Recorded as Fitzpatrick I. A male patient in their 60s: 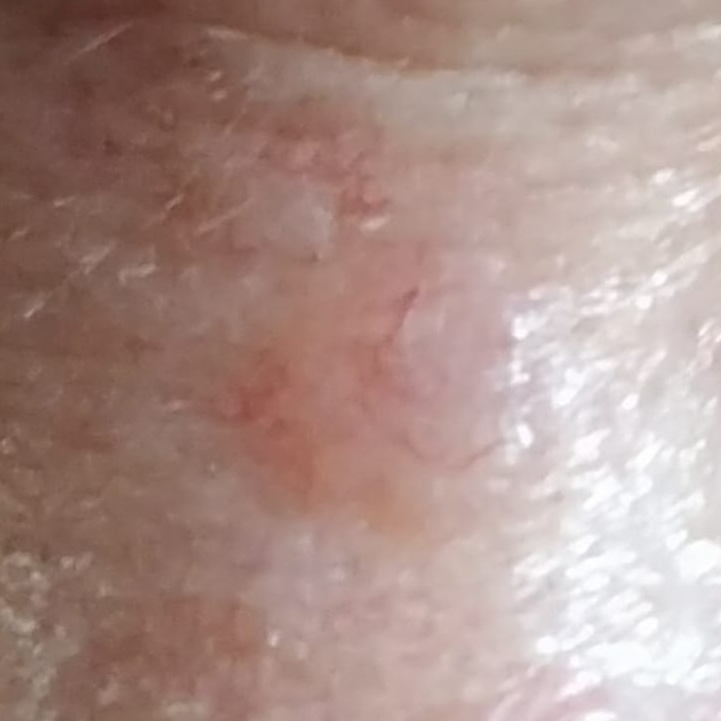Findings:
The lesion involves the face. The lesion is roughly 5 by 5 mm. Per patient report, the lesion is elevated and has grown.
Conclusion:
The biopsy diagnosis was a malignancy — a basal cell carcinoma.